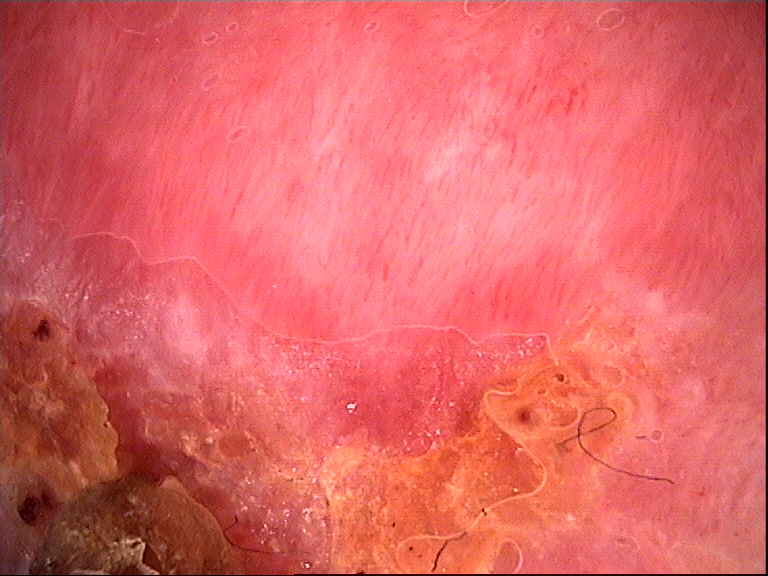image: dermoscopy
lesion_type:
  main_class: keratinocytic
diagnosis:
  name: squamous cell carcinoma
  code: scc
  malignancy: malignant
  super_class: non-melanocytic
  confirmation: histopathology